The affected area is the arm and leg. The subject is male. An image taken at an angle: 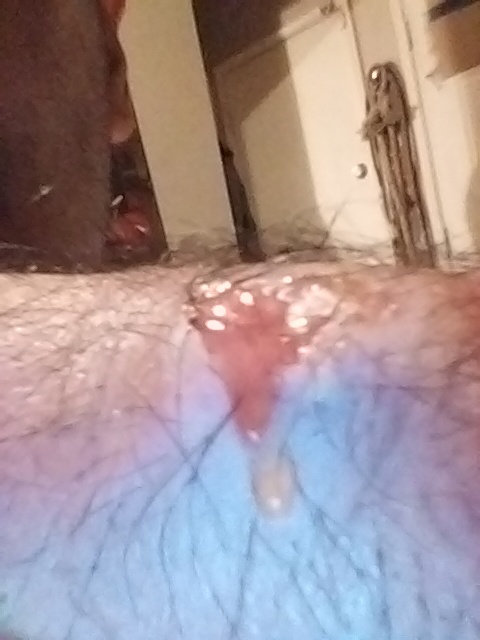Diagnostic features were not clearly distinguishable in this photograph.
The lesion is associated with bleeding, bothersome appearance and pain.